The photograph was taken at a distance — 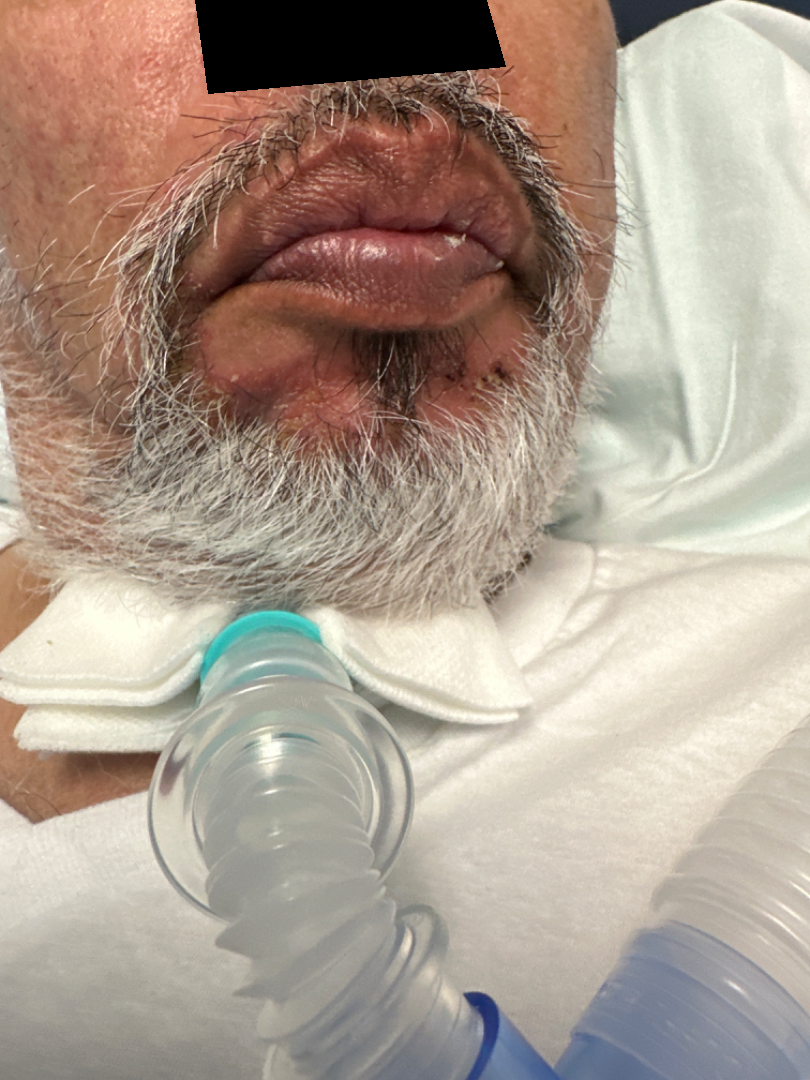Impression: On photographic review by a dermatologist, Seborrheic Dermatitis (most likely).